A dermatoscopic image of a skin lesion:
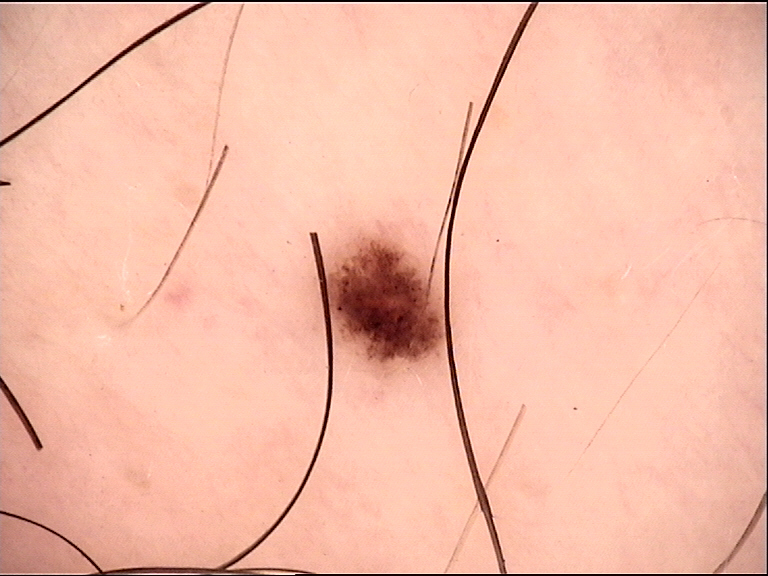Impression: Consistent with a benign lesion — a dysplastic junctional nevus.